A dermoscopic photograph of a skin lesion.
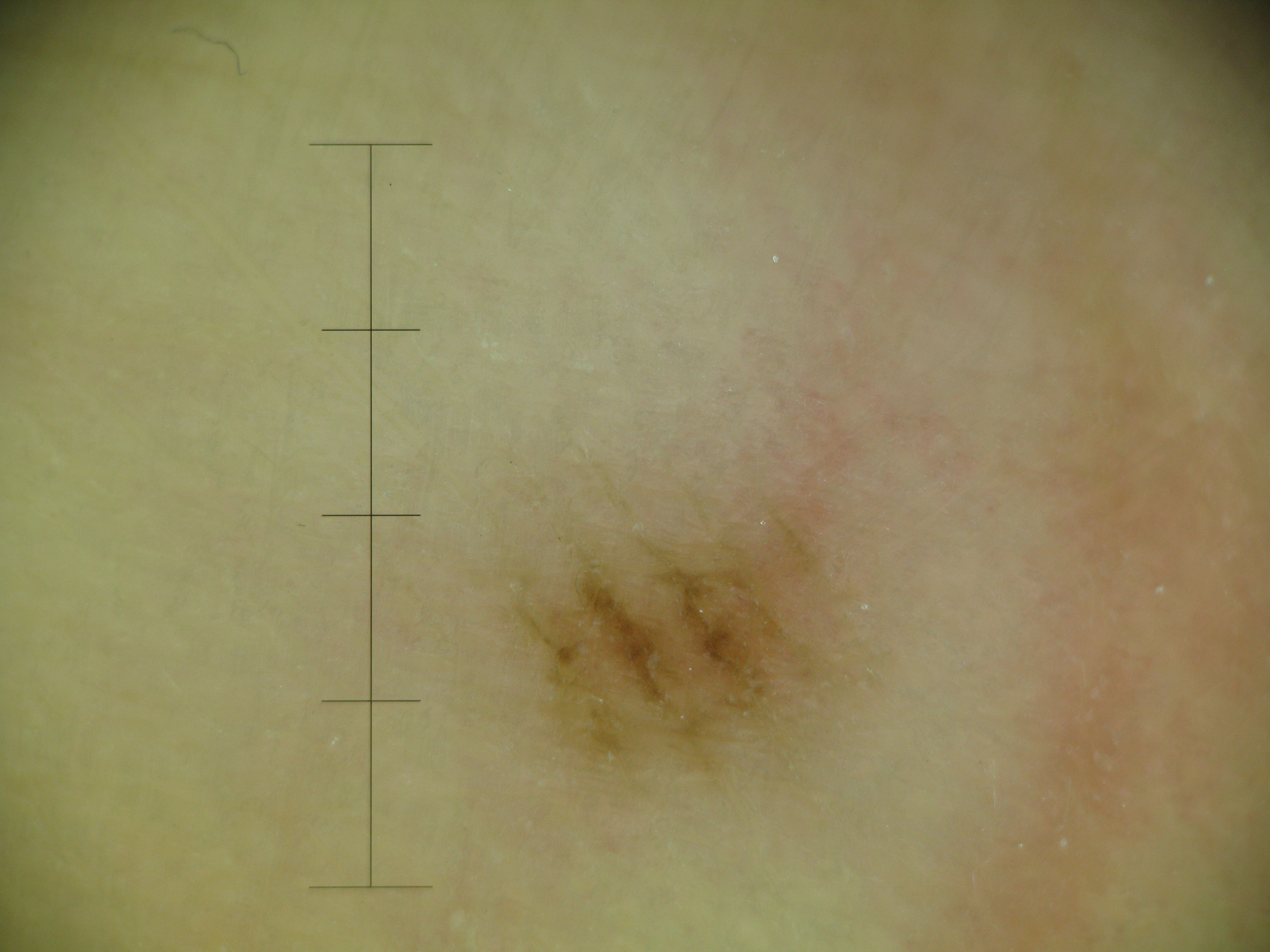Conclusion:
The diagnostic label was a banal lesion — an acral junctional nevus.